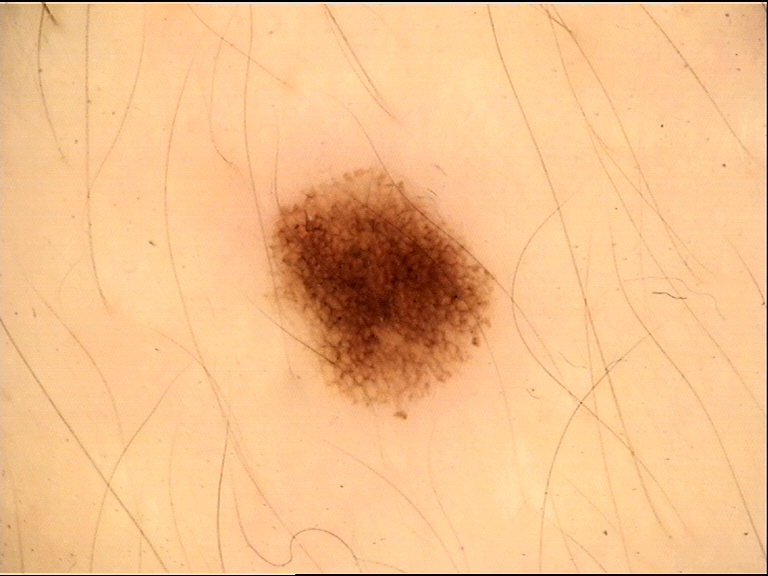Case:
- imaging · dermoscopy
- class · dysplastic junctional nevus (expert consensus)